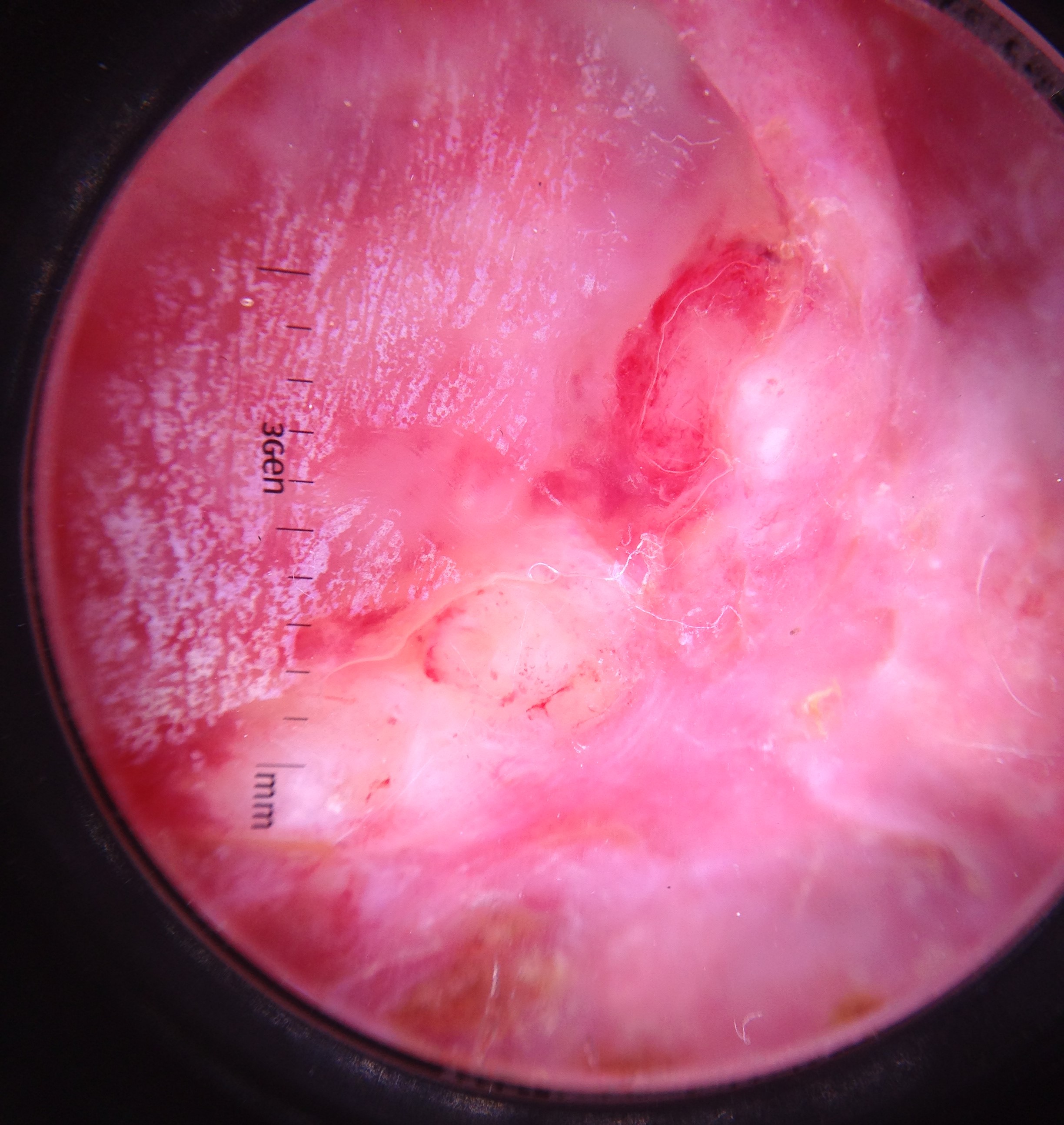A skin lesion imaged with a dermatoscope.
The biopsy diagnosis was a squamous cell carcinoma.